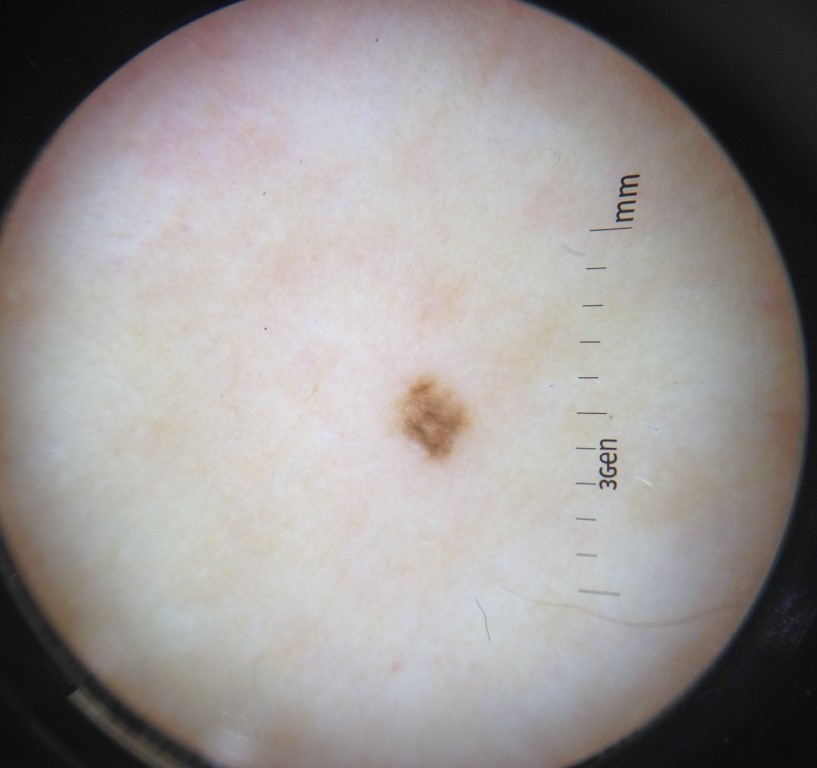The diagnostic label was a benign lesion — a dysplastic junctional nevus.